A dermoscopy image of a single skin lesion: 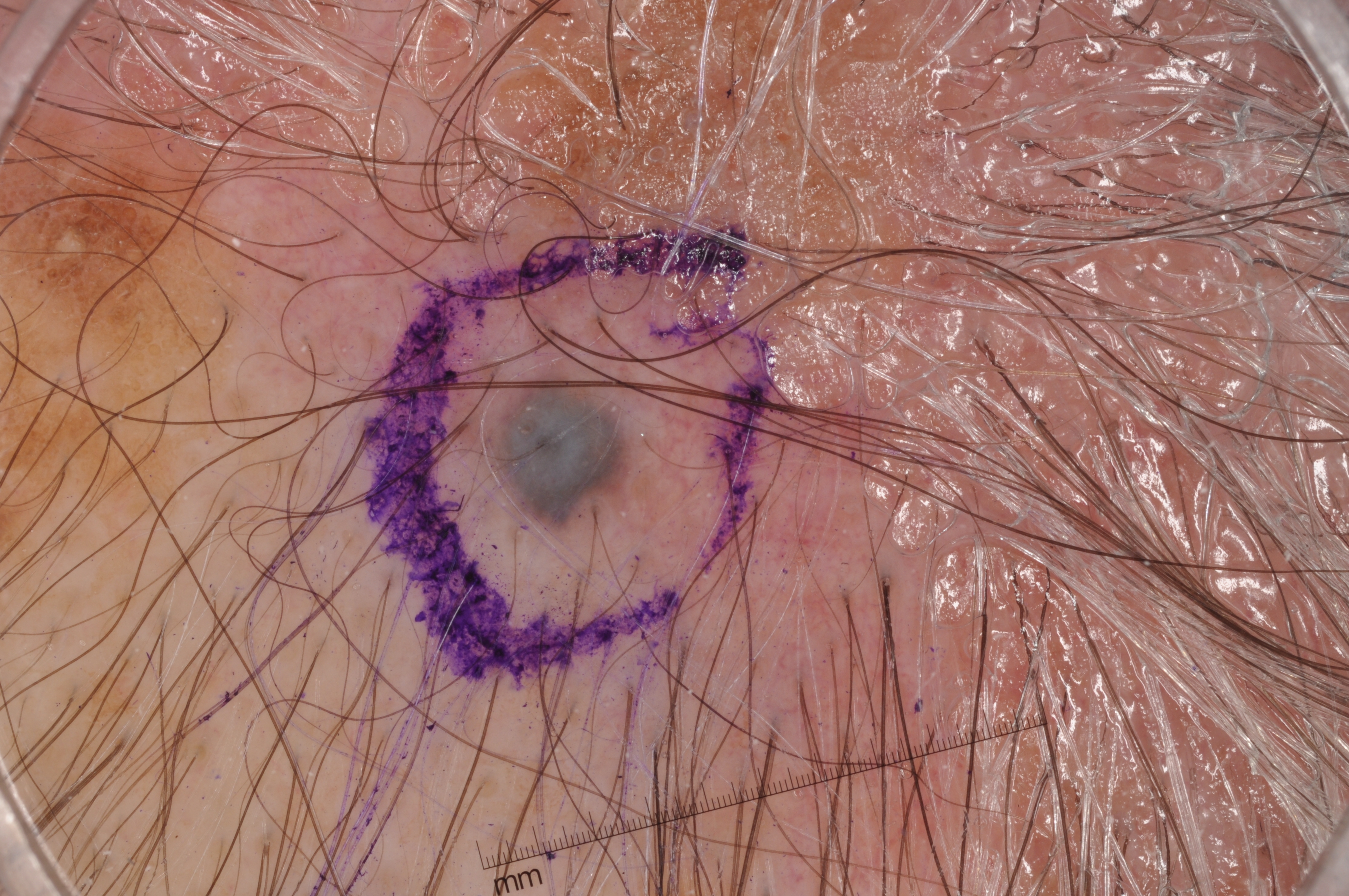{
  "dermoscopic_features": {
    "present": [
      "milia-like cysts"
    ],
    "absent": [
      "streaks",
      "negative network",
      "pigment network"
    ]
  },
  "lesion_extent": {
    "approx_field_fraction_pct": 1
  },
  "lesion_location": {
    "bbox_xyxy": [
      484,
      387,
      629,
      531
    ]
  },
  "diagnosis": {
    "name": "melanocytic nevus",
    "malignancy": "benign",
    "lineage": "melanocytic",
    "provenance": "clinical"
  }
}